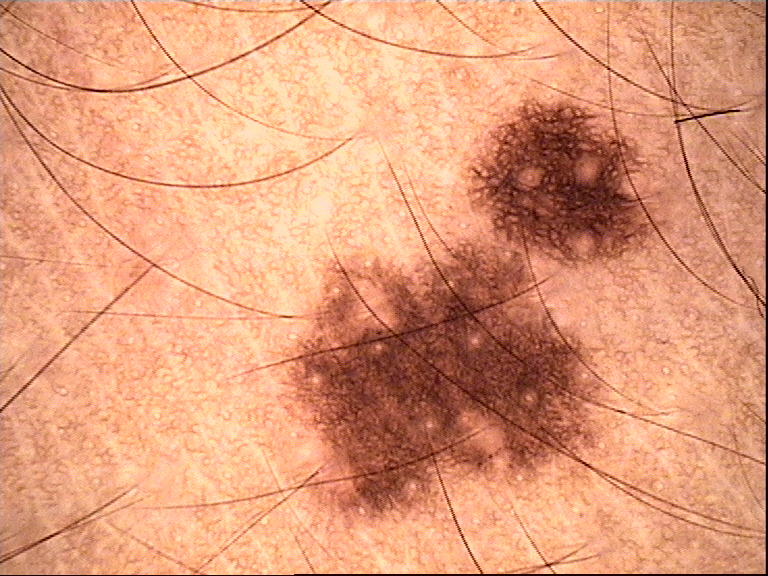A dermoscopic photograph of a skin lesion. Consistent with a dysplastic junctional nevus.